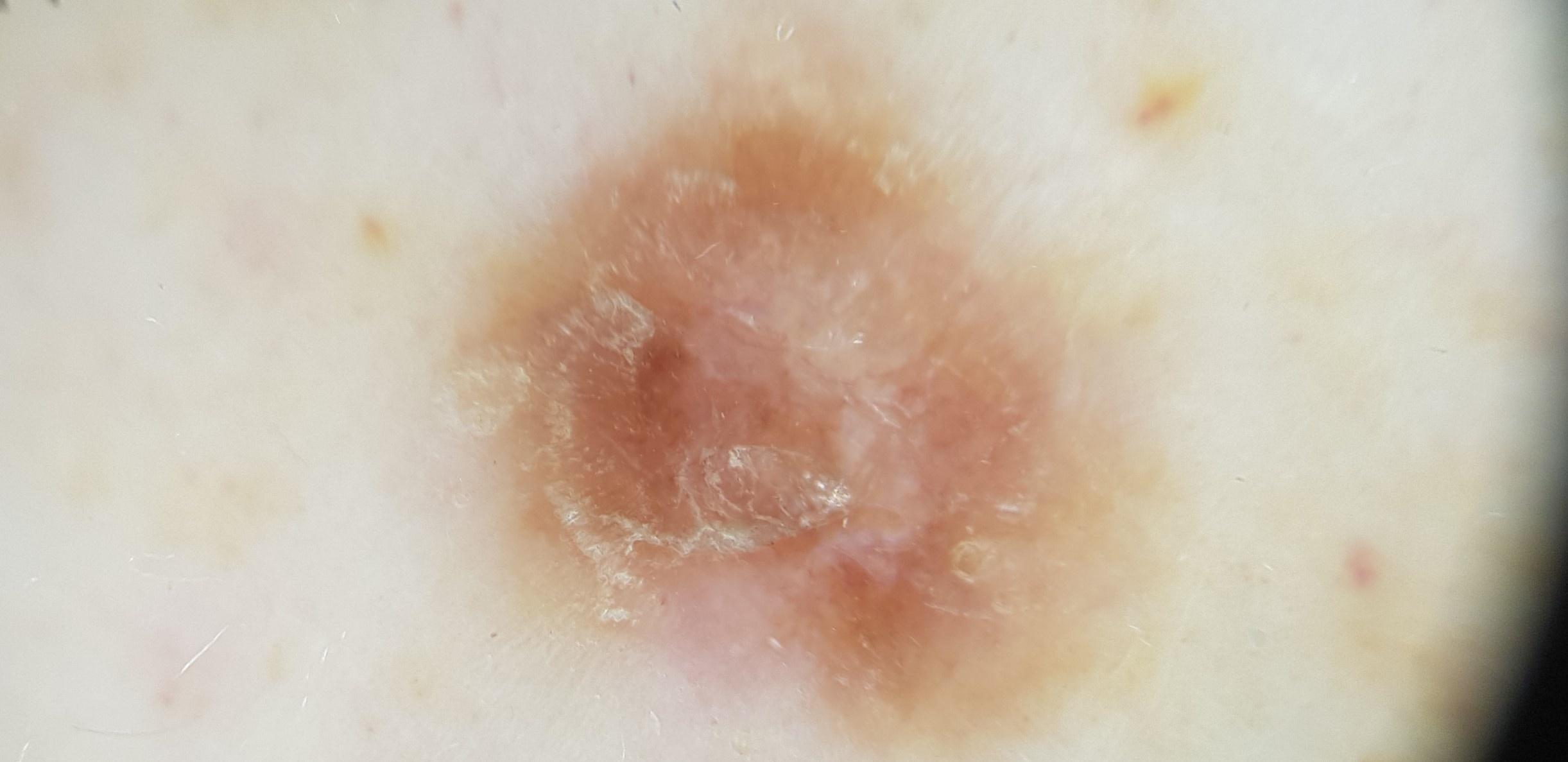Q: Patient demographics?
A: male, aged 58-62
Q: What is the patient's skin type?
A: II
Q: What is the imaging modality?
A: contact-polarized dermoscopy
Q: What is the anatomic site?
A: a lower extremity
Q: What did the workup show?
A: Dermatofibroma (biopsy-proven)